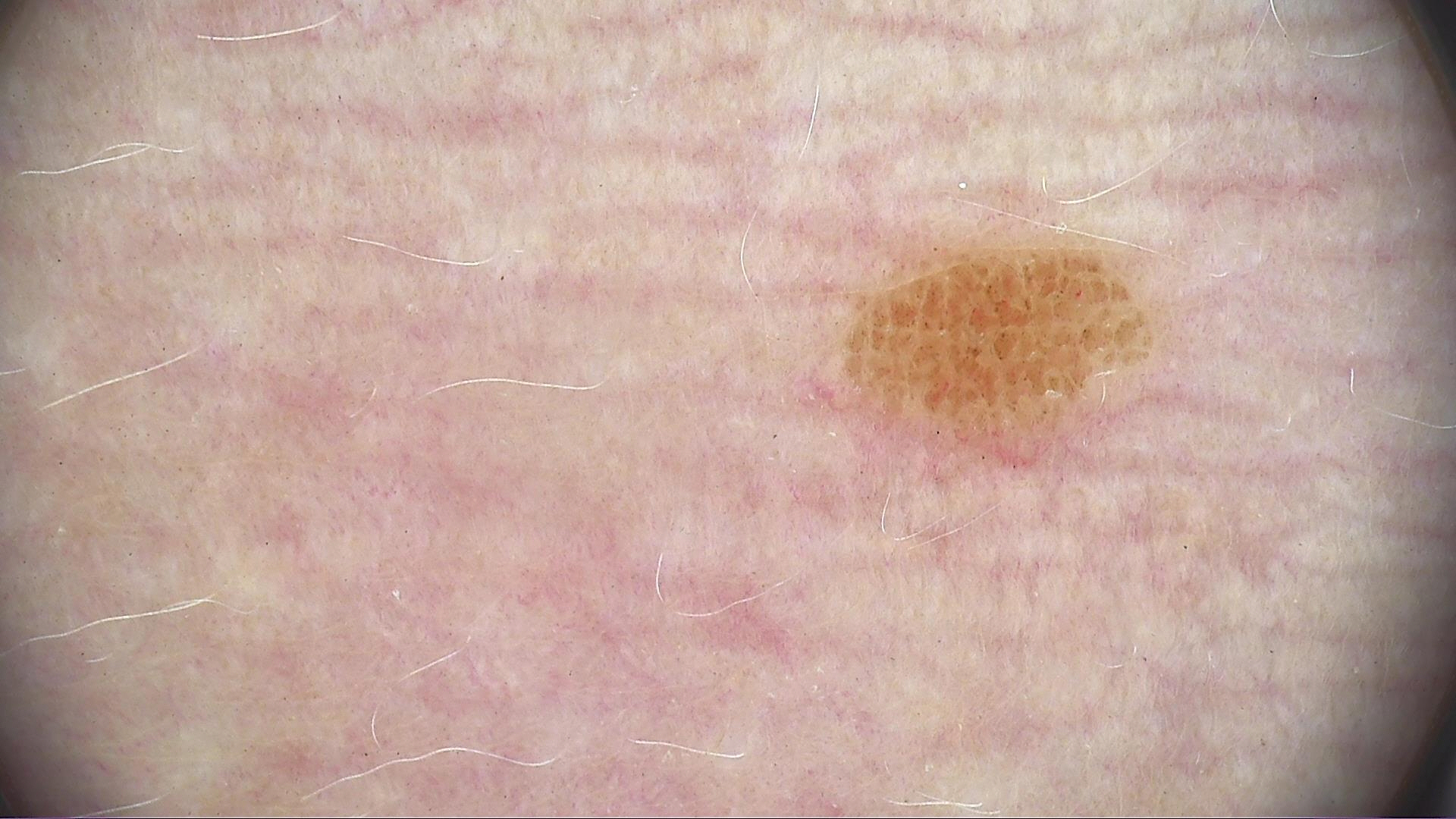Findings: A skin lesion imaged with a dermatoscope. The architecture is that of a banal lesion. Conclusion: The diagnosis was a compound nevus.